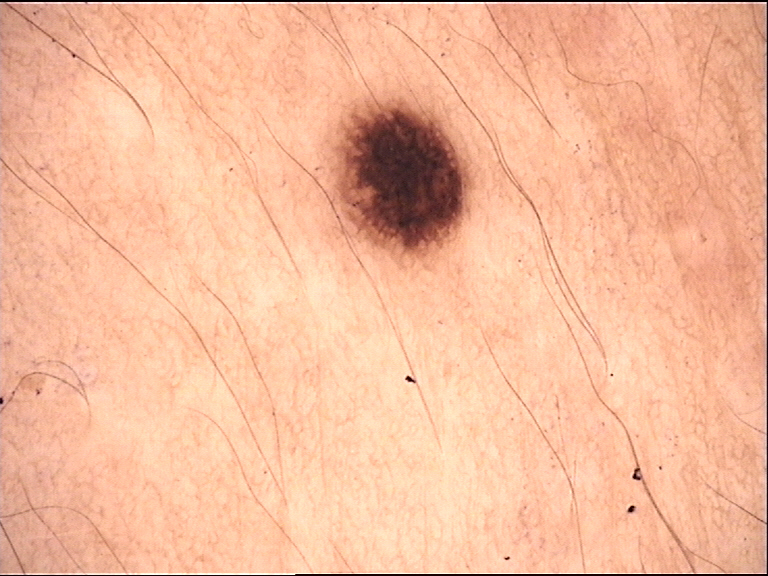classification: banal, assessment: junctional nevus (expert consensus).